The condition has been present for less than one week. The subject is 18–29, female. The contributor notes the lesion is raised or bumpy, rough or flaky and fluid-filled. An image taken at a distance. The patient described the issue as a rash. The lesion involves the arm.
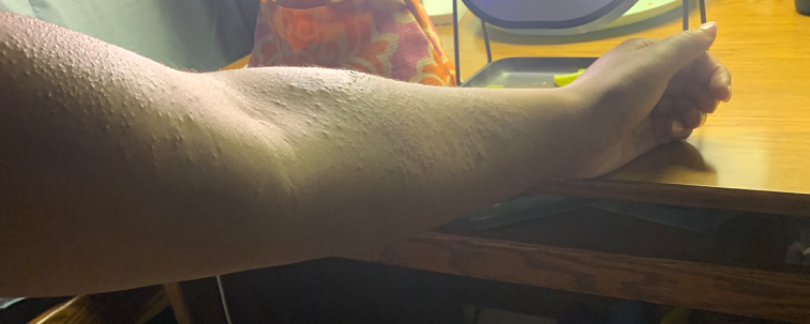Case summary:
- differential diagnosis — single-reviewer assessment: consistent with Allergic Contact Dermatitis